A moderate number of moles by the patient's own estimate. On a questionnaire the patient reported a personal history of skin cancer. A female patient 50 years of age. A dermoscopy image of a skin lesion. Imaged for a research study, with no referral diagnosis recorded. The patient says their skin reddens with sun exposure — 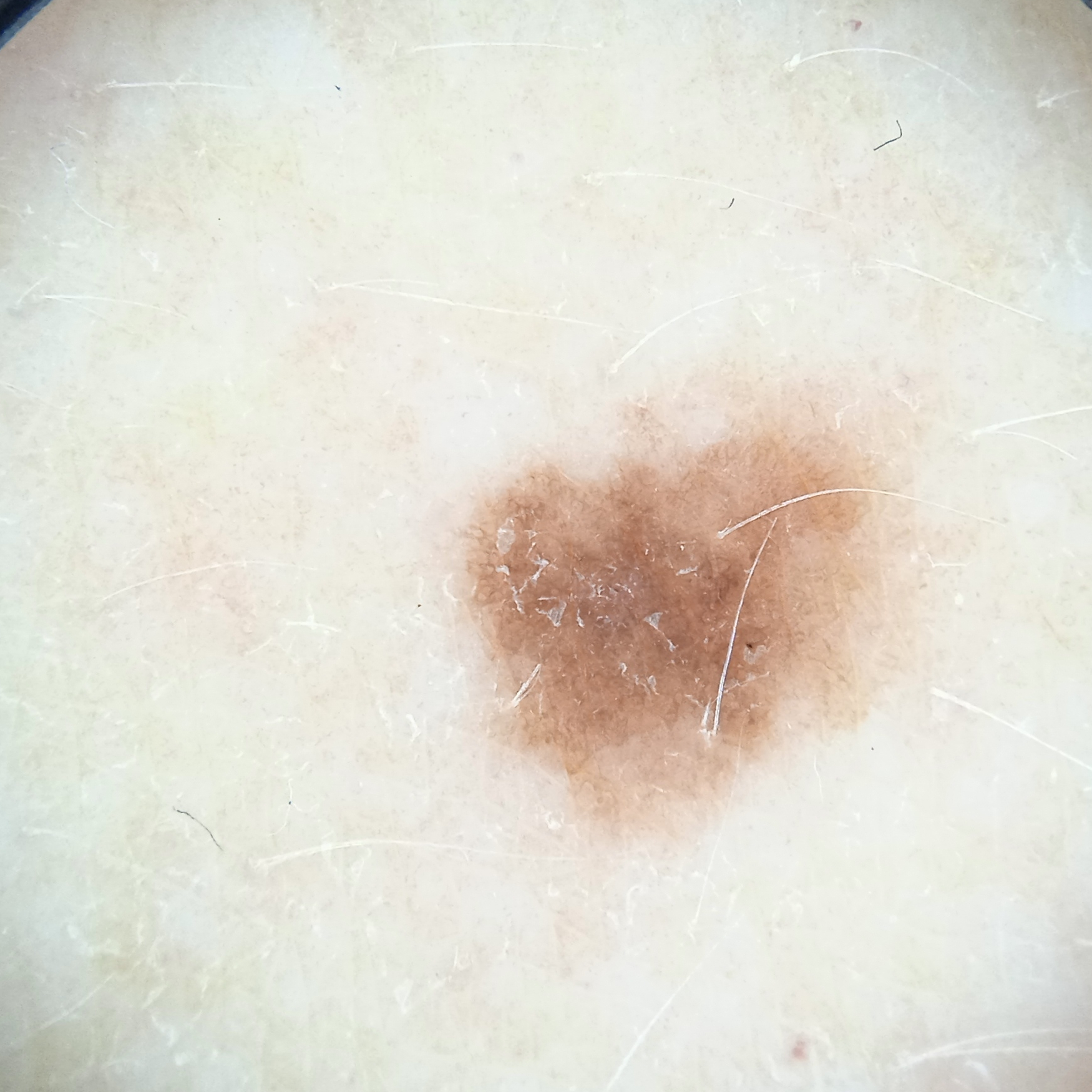Conclusion:
The dermatologists' assessment was a melanocytic nevus.